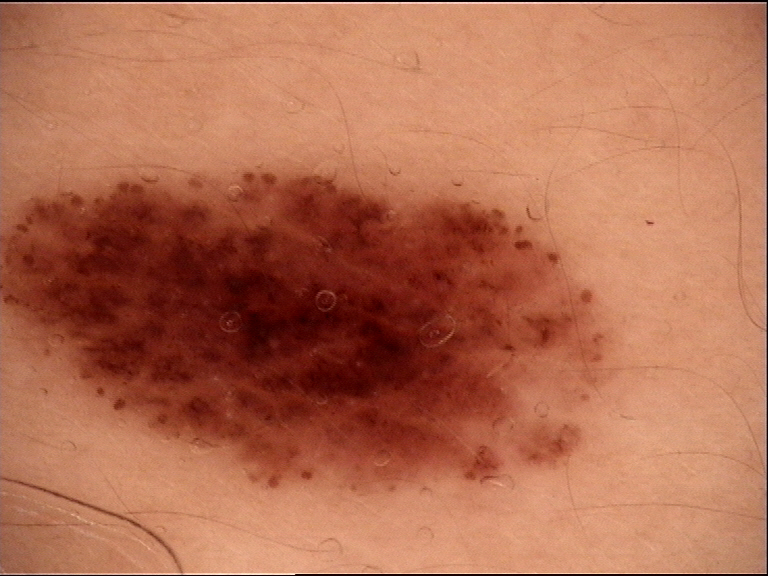Impression: The diagnosis was a dysplastic junctional nevus.